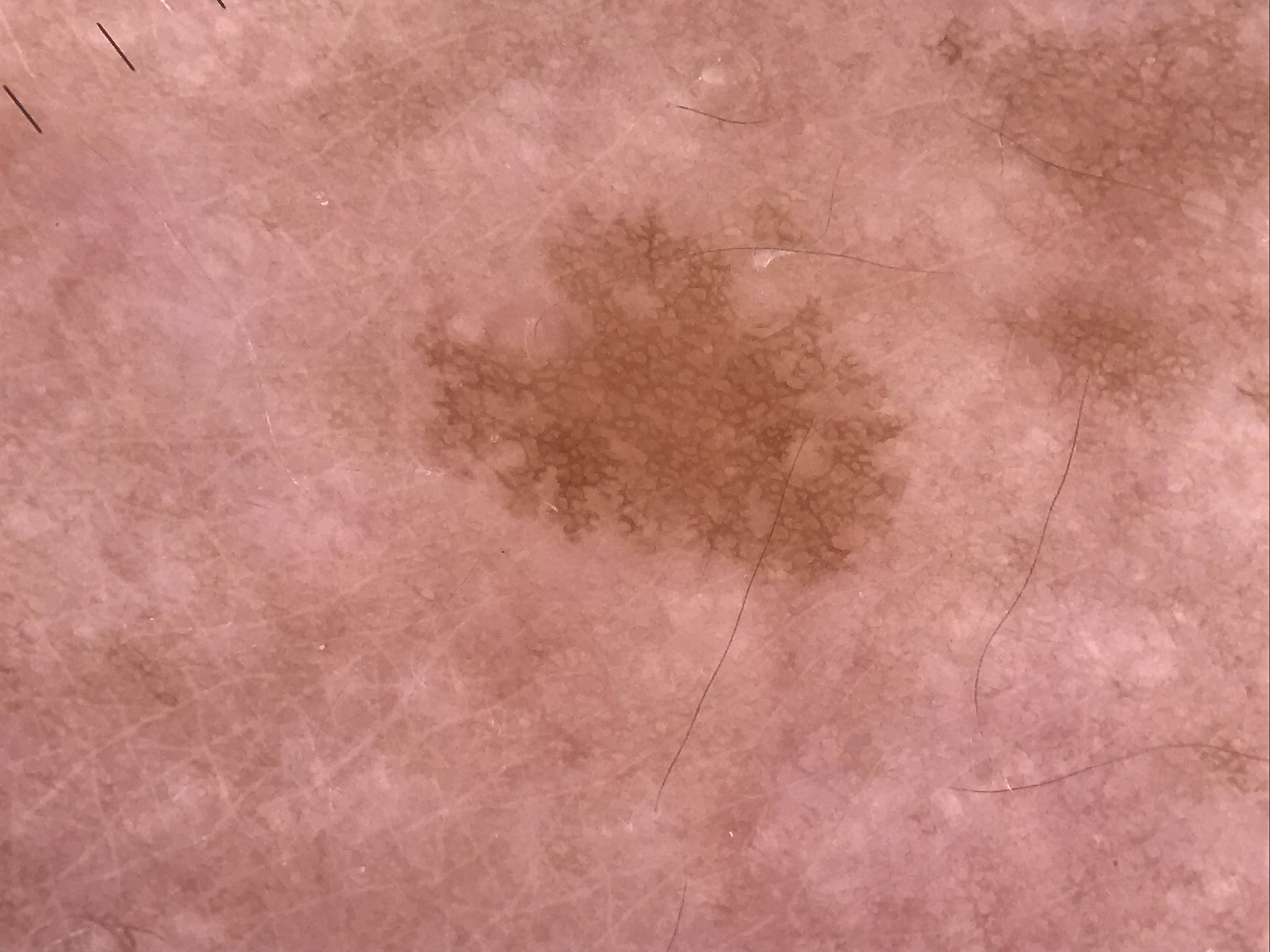Case: Dermoscopy of a skin lesion. Impression: The diagnosis was a benign lesion — a solar lentigo.